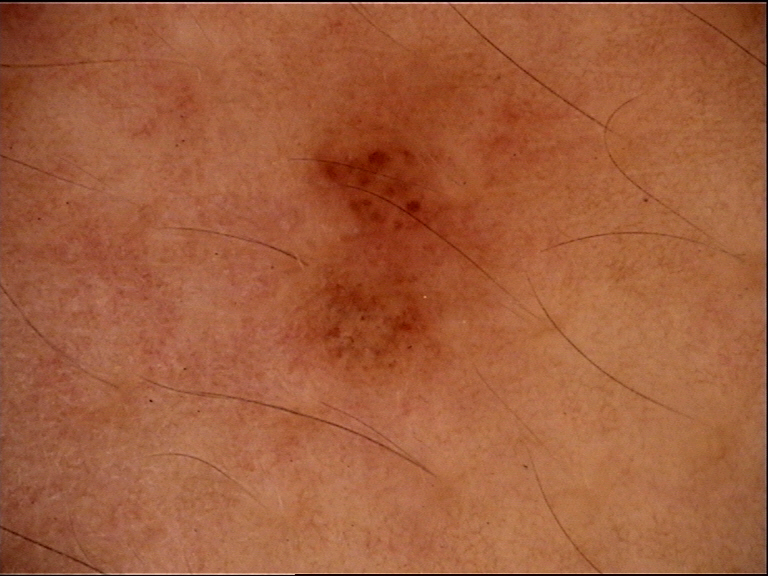| field | value |
|---|---|
| image type | dermoscopy |
| assessment | dysplastic compound nevus (expert consensus) |